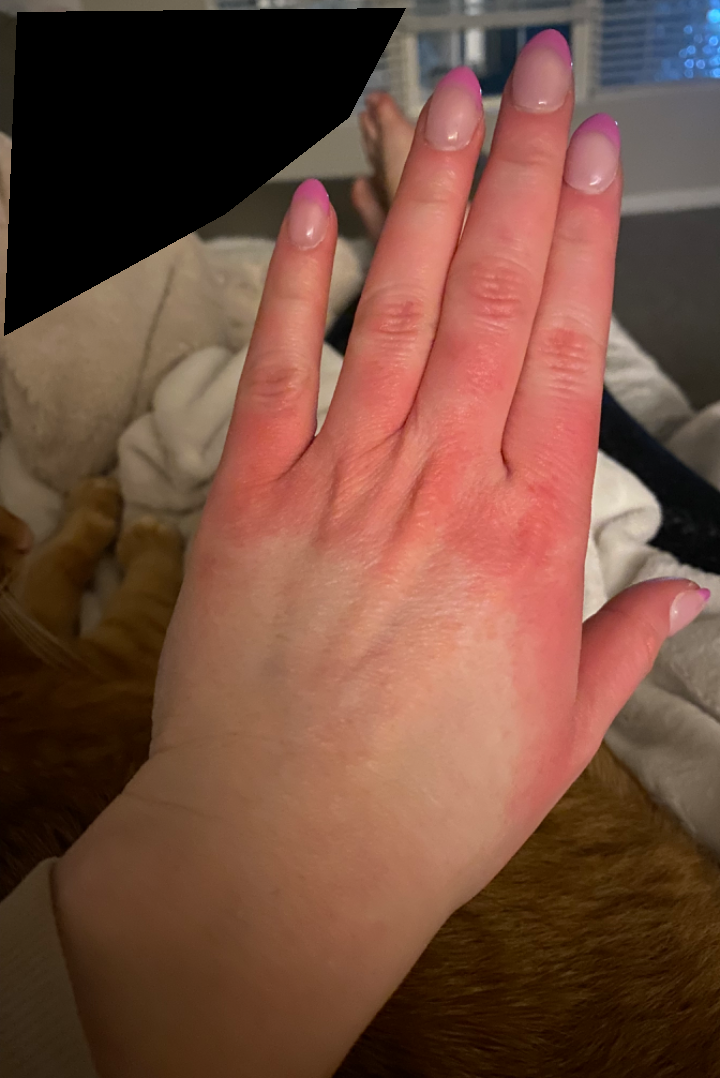On remote dermatologist review, Irritant Contact Dermatitis (favored); Acral erythema (considered); Allergic Contact Dermatitis (considered).